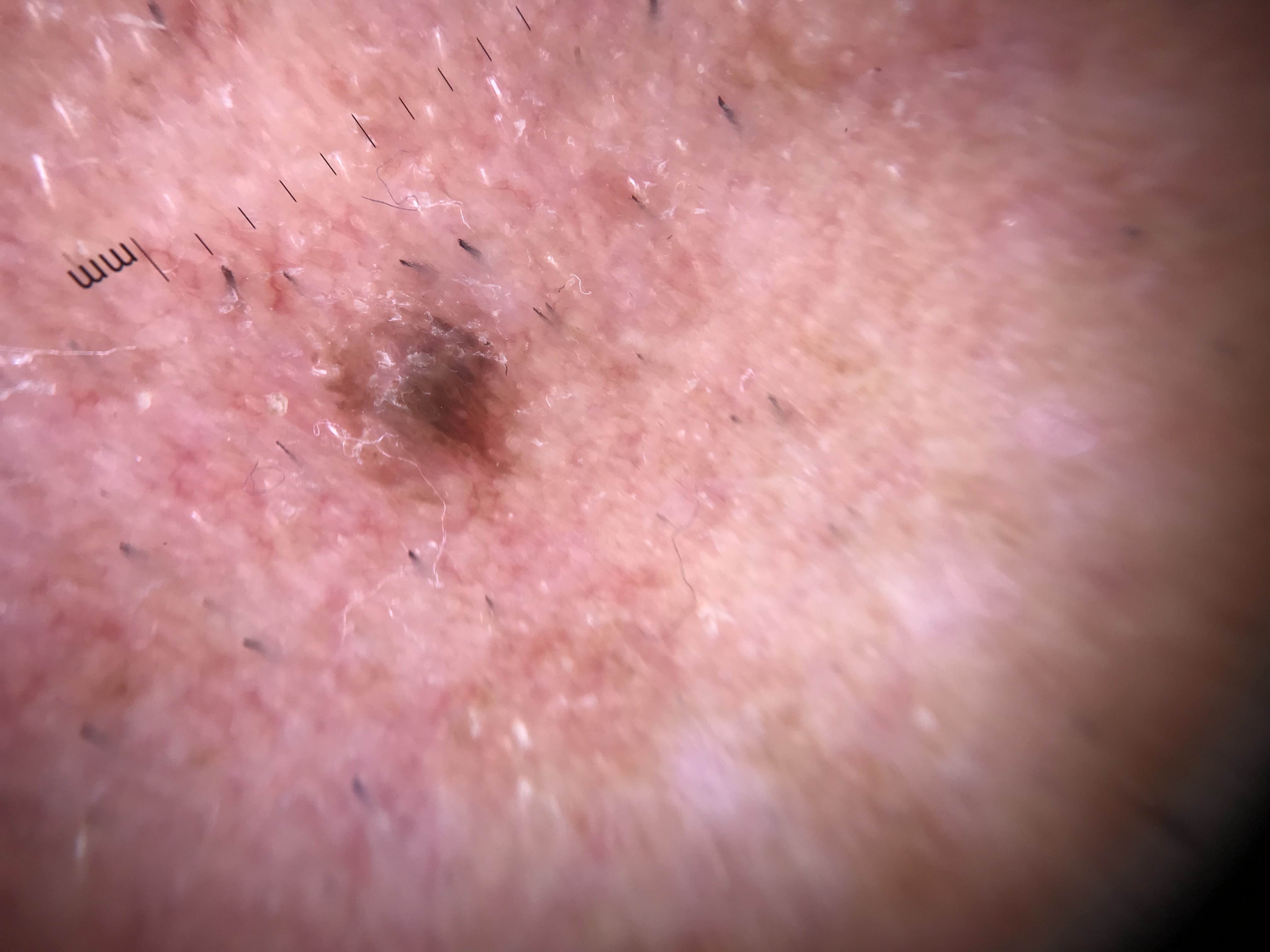A dermoscopic image of a skin lesion.
The architecture is that of a keratinocytic lesion.
The diagnostic label was a benign lesion — a seborrheic keratosis.